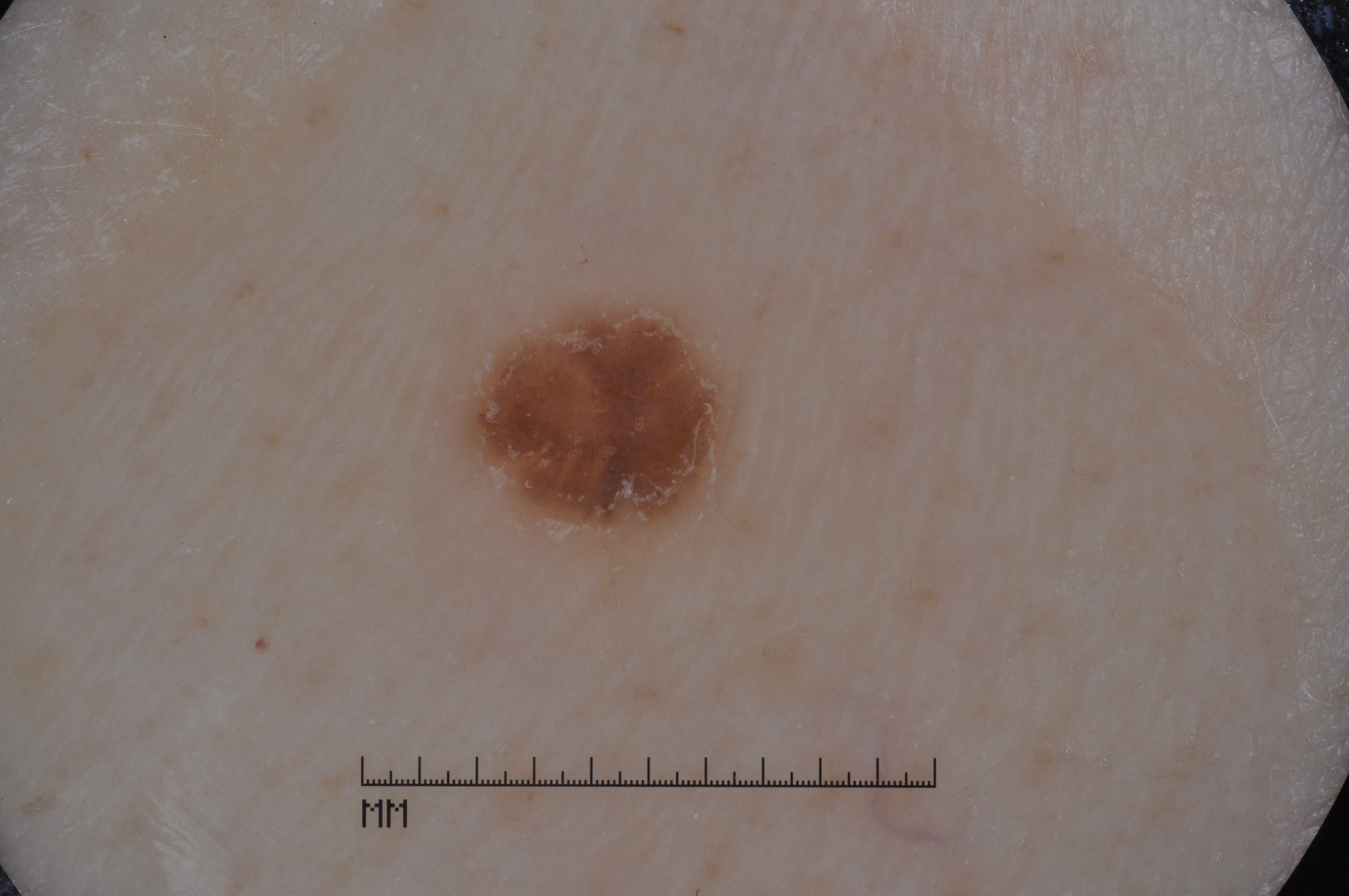image = dermoscopy
subject = male, approximately 50 years of age
lesion bbox = [454,299,742,551]
dermoscopic features = milia-like cysts
impression = a seborrheic keratosis, a benign skin lesion